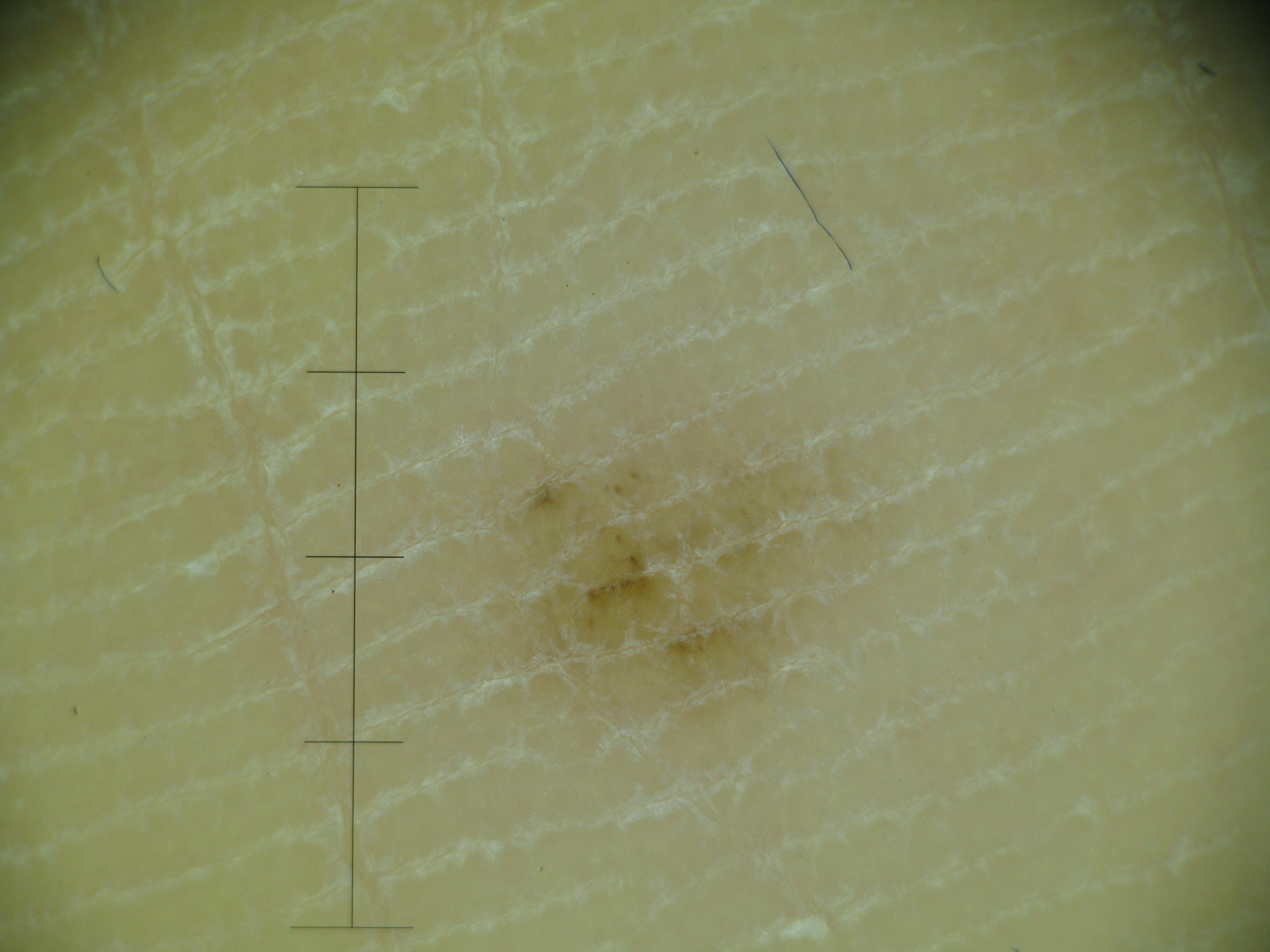A dermoscopic close-up of a skin lesion. The architecture is that of a banal lesion. Diagnosed as an acral junctional nevus.